On a questionnaire the patient reported a history of sunbed use. Acquired for a research image collection, with no referral diagnosis. The patient says their skin reddens with sun exposure. A female subject age 26. The patient describes having numerous moles.
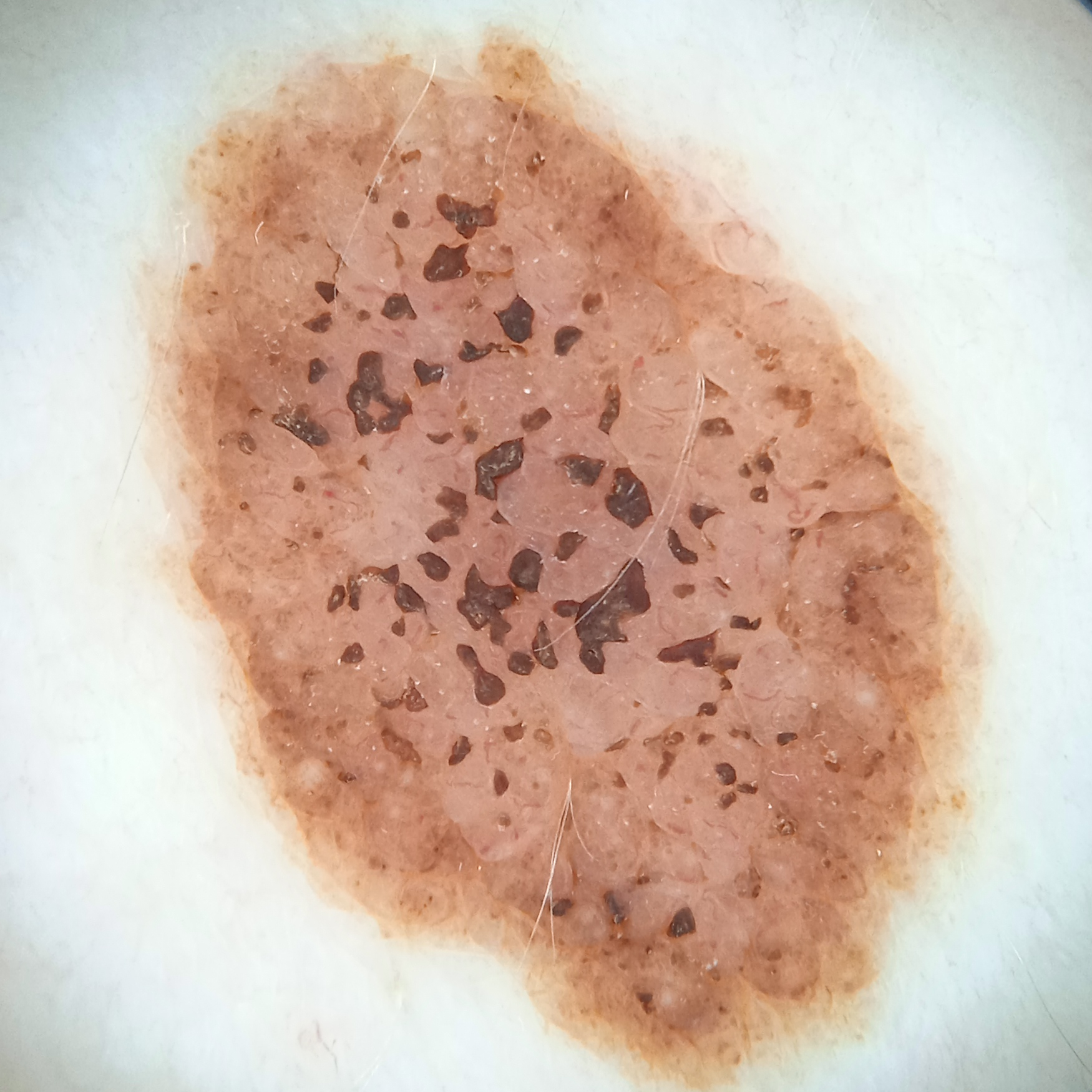Q: How large is the lesion?
A: 12.1 mm
Q: What was the diagnosis?
A: melanocytic nevus (dermatologist consensus)